Dermoscopy of a skin lesion.
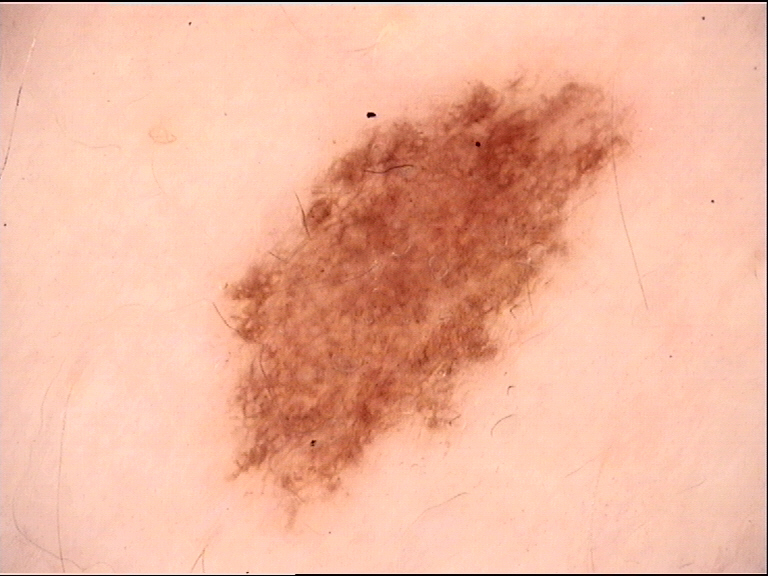Diagnosed as a dysplastic junctional nevus.